This is a close-up image: 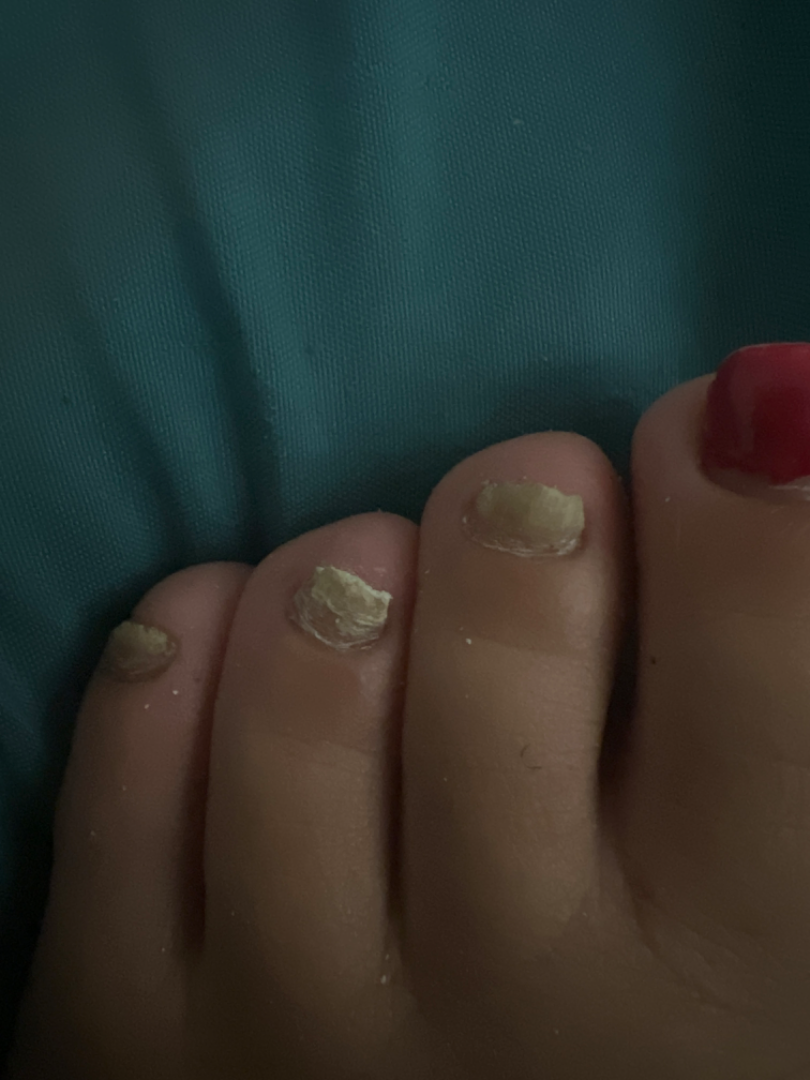• differential diagnosis · Onychomycosis (54%); Onychodystrophy (23%); Psoriasis (23%)